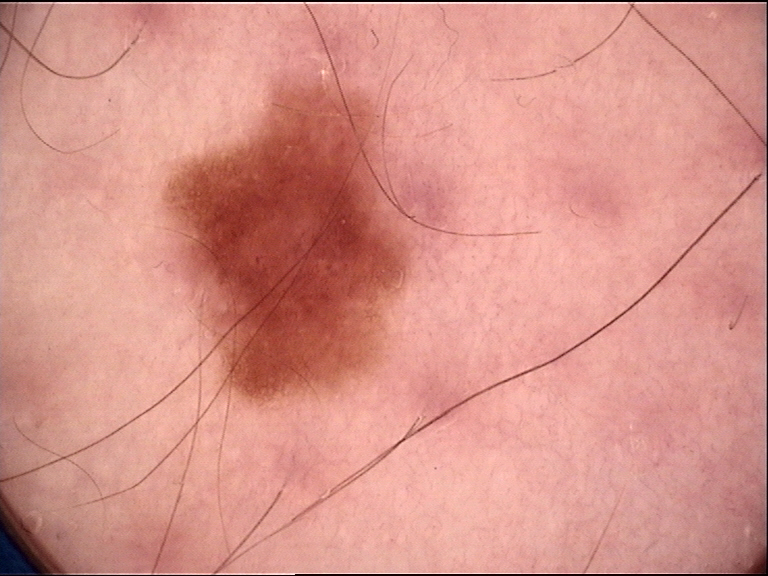Dermoscopy of a skin lesion.
The diagnostic label was a dysplastic junctional nevus.